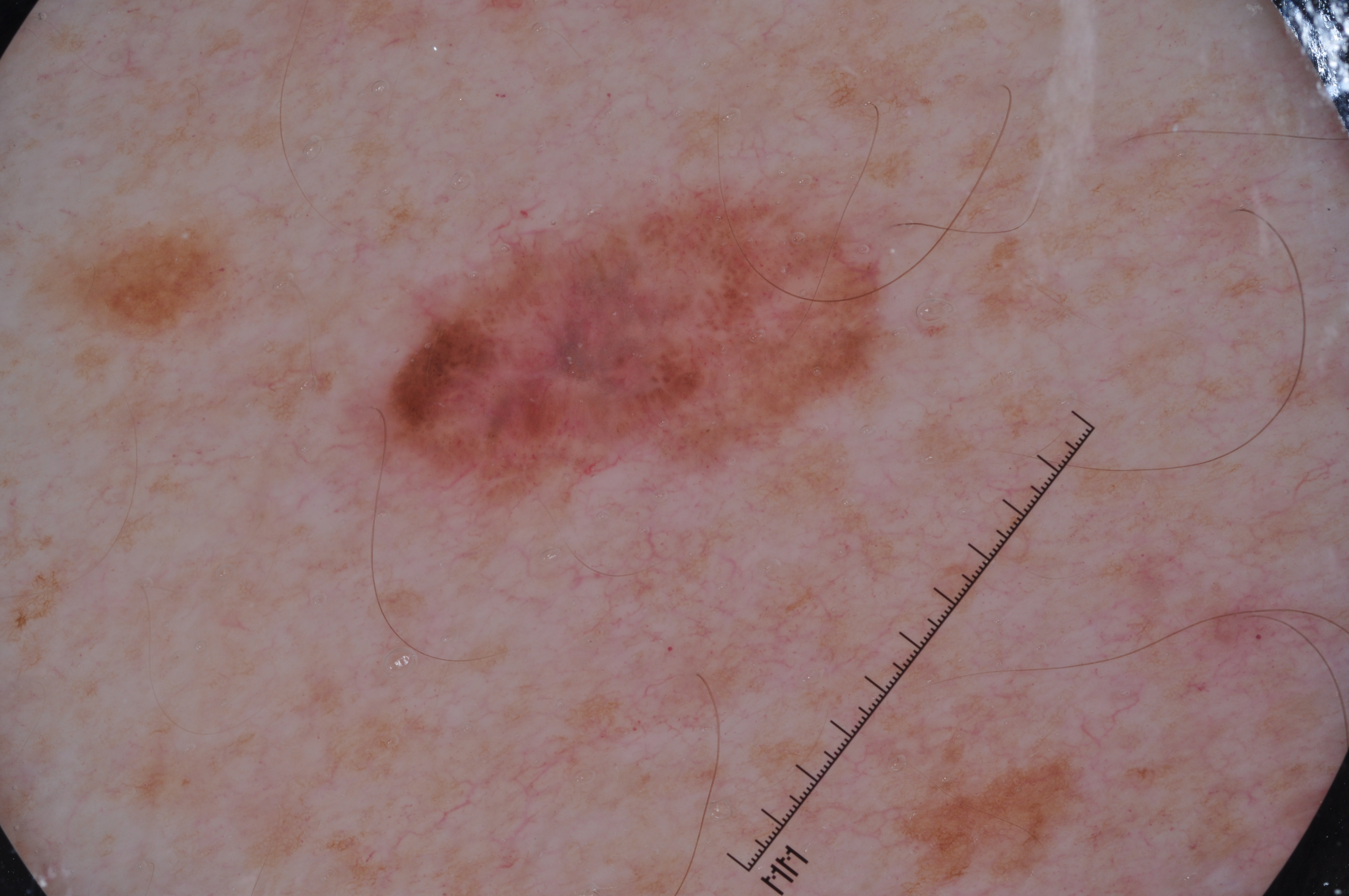A male patient aged 48 to 52.
A dermoscopic close-up of a skin lesion.
A moderately sized lesion.
With coordinates (x1, y1, x2, y2), the lesion spans 369 189 885 497.
Dermoscopic review identifies negative network; no streaks, milia-like cysts, or pigment network.
Confirmed on histopathology as a melanoma, a malignant skin lesion.